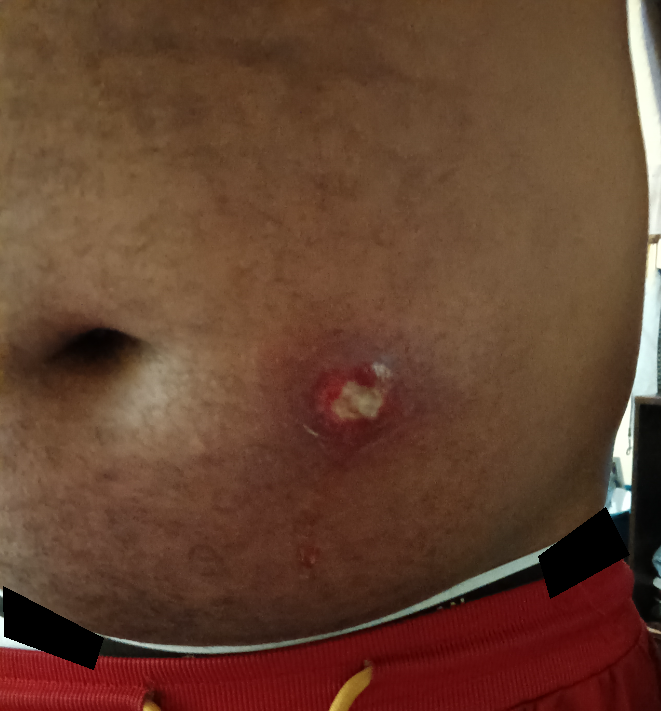Male subject, age 30–39. Fitzpatrick V. The patient considered this a rash. The lesion is described as raised or bumpy. The front of the torso is involved. The contributor notes the condition has been present for less than one week. A close-up photograph. The contributor notes enlargement, darkening and bleeding. On dermatologist assessment of the image, most consistent with Abscess.